An image taken at a distance: 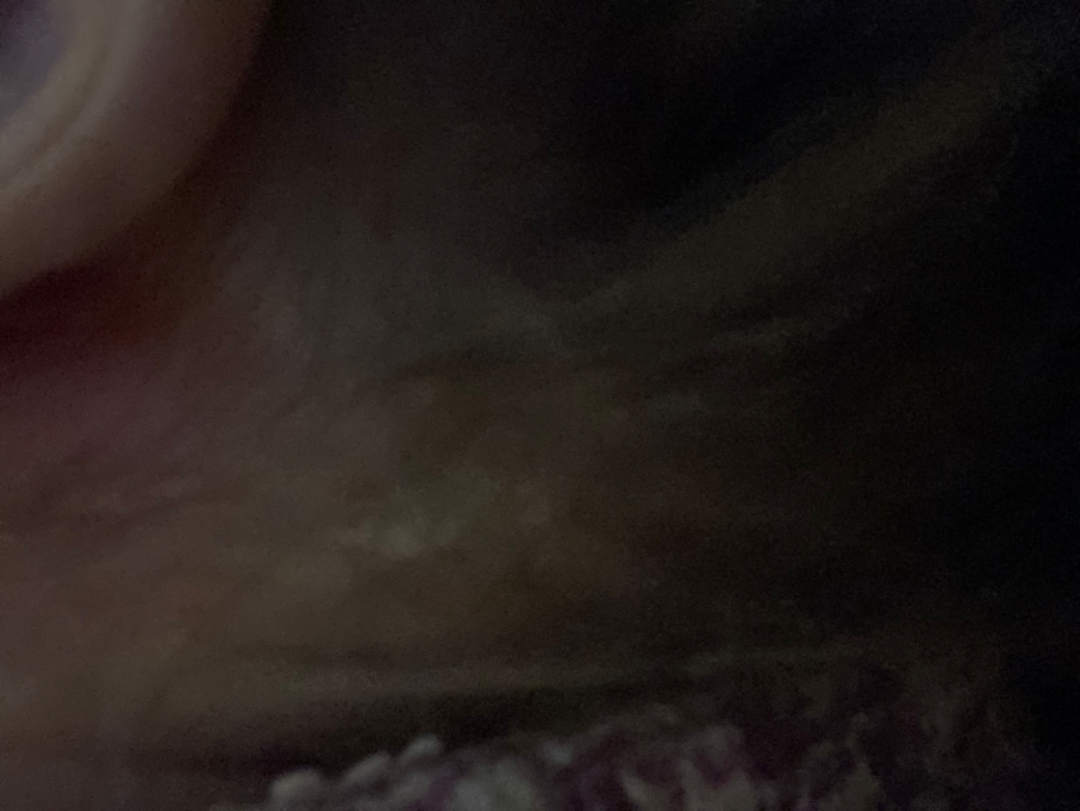<case>
<assessment>indeterminate from the photograph</assessment>
</case>